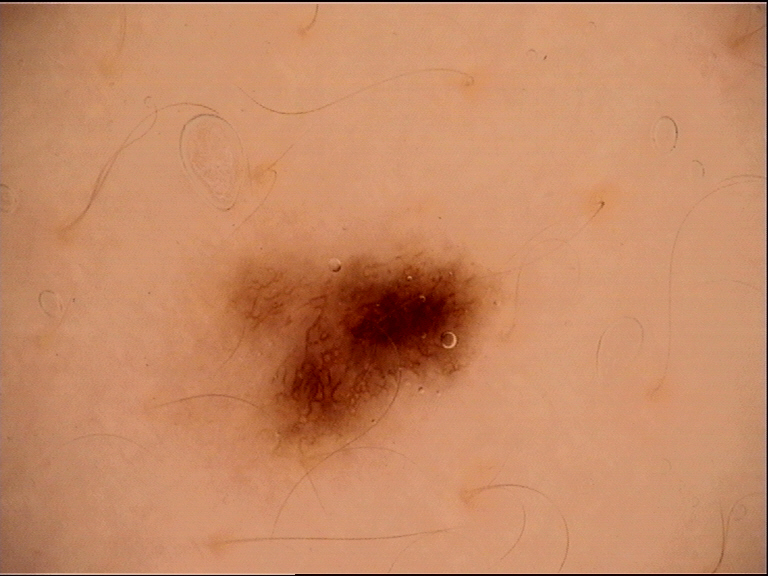A dermoscopy image of a single skin lesion.
Classified as a benign lesion — a dysplastic junctional nevus.